The affected area is the leg. Close-up view:
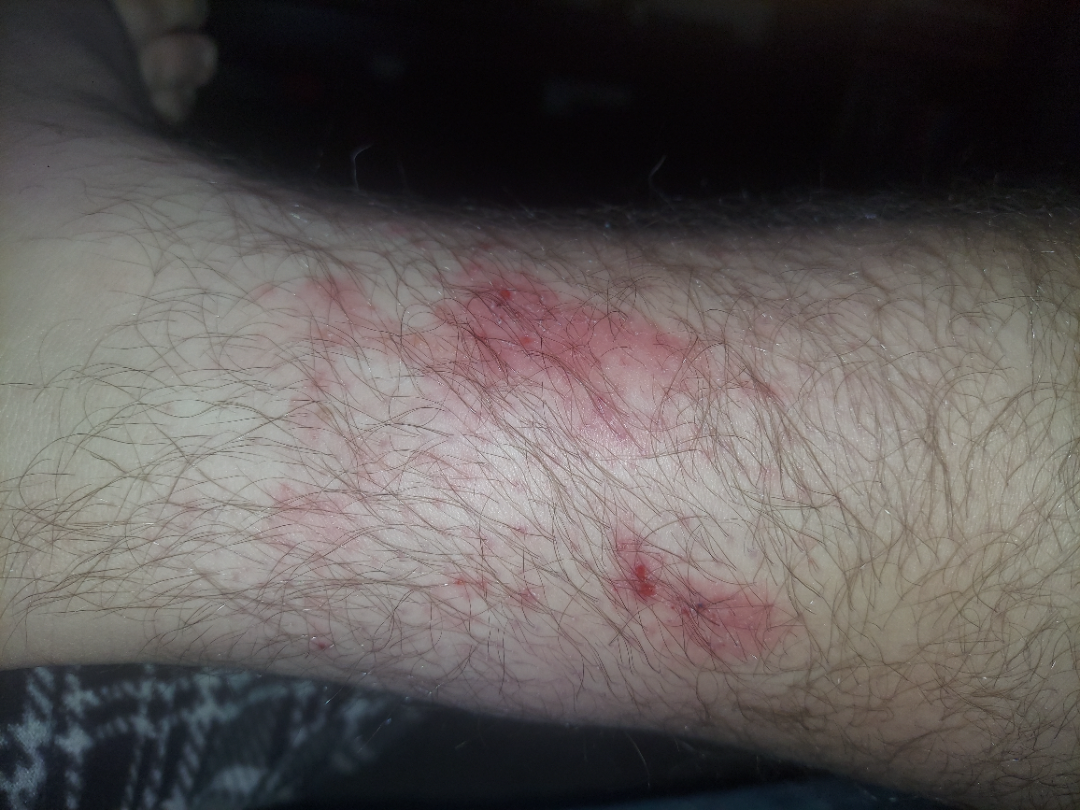assessment: the differential is split between Eczema and Allergic Contact Dermatitis